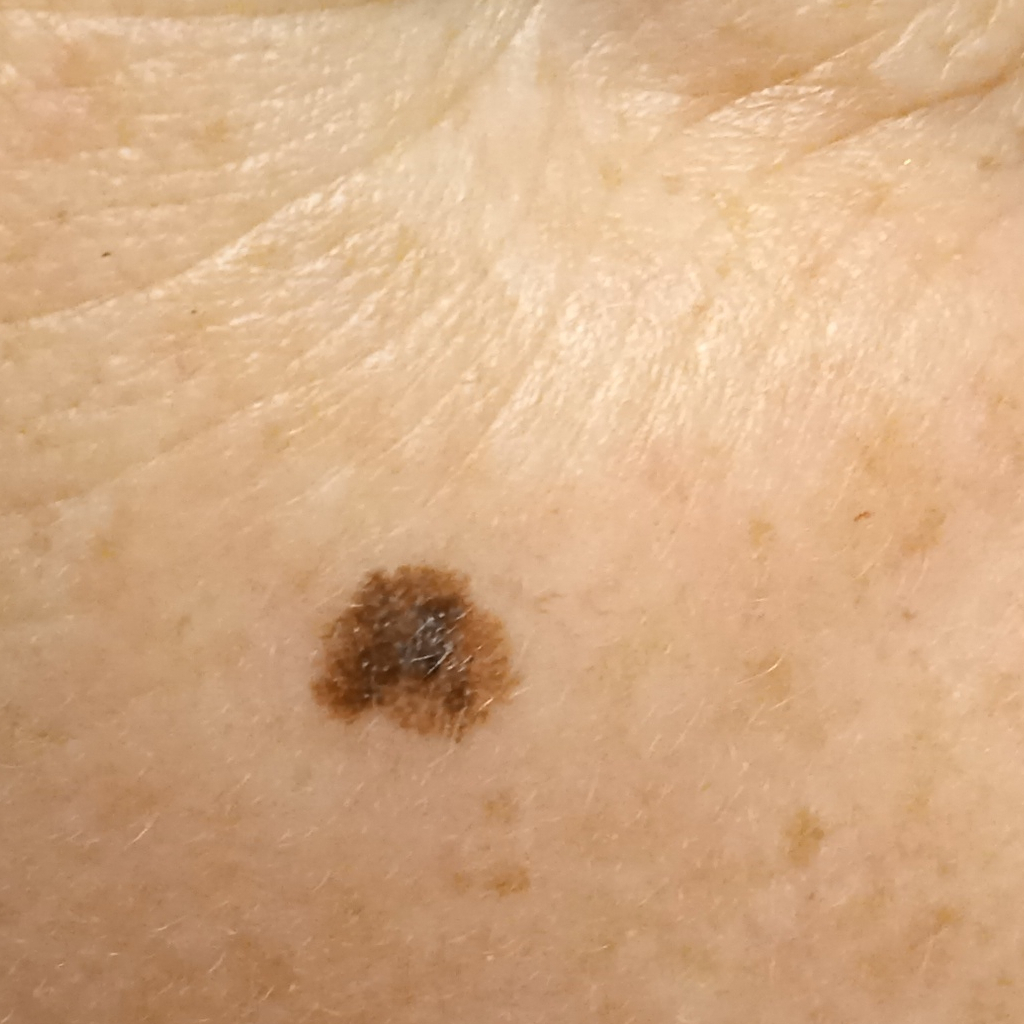| field | value |
|---|---|
| nevus count | a moderate number of melanocytic nevi |
| sun reaction | skin reddens with sun exposure |
| risk factors | a personal history of skin cancer, no immunosuppression, no personal history of cancer |
| image | clinical photograph |
| referral | clinical suspicion of melanoma |
| subject | female, age 50 |
| anatomic site | the face |
| size | 7 mm |
| diagnostic label | melanoma (biopsy-proven) |